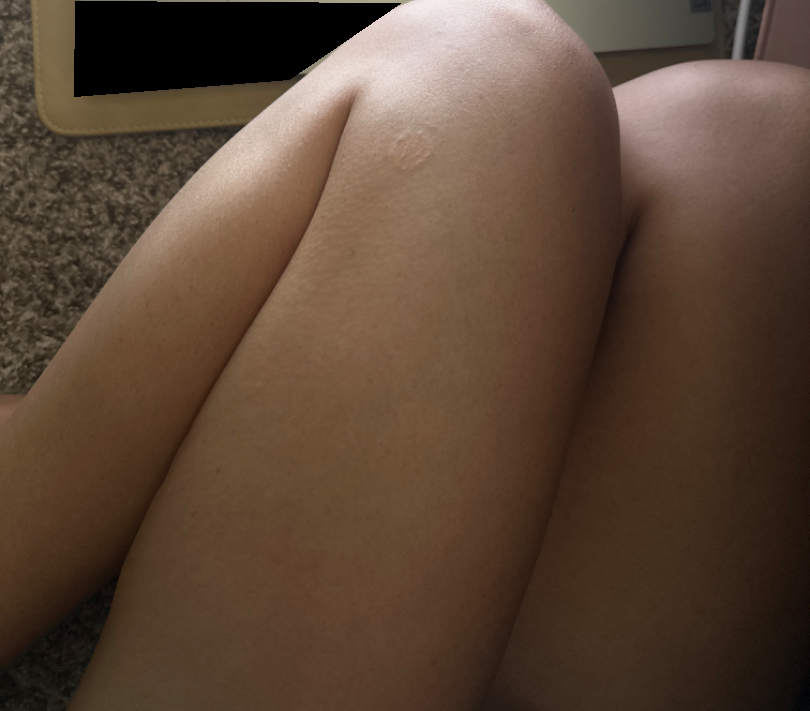The photo was captured at a distance.
Skin tone: Fitzpatrick phototype IV.
On dermatologist assessment of the image, the impression was split between Tinea, Eczema and Psoriasis.